Reported lesion symptoms include bothersome appearance, burning and itching. An image taken at a distance. The condition has been present for less than one week. The lesion is described as fluid-filled and raised or bumpy. The patient considered this a rash. The affected area is the leg. Lay reviewers estimated Monk Skin Tone 2–3.
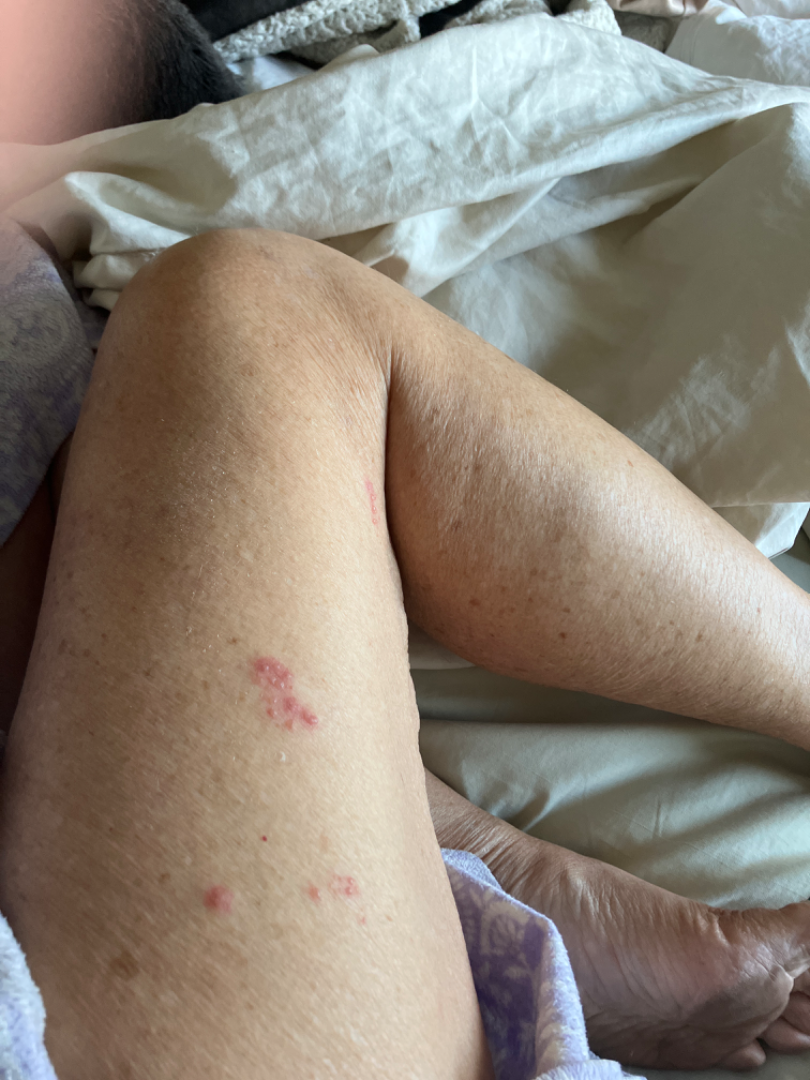Q: What was the assessment?
A: could not be assessed